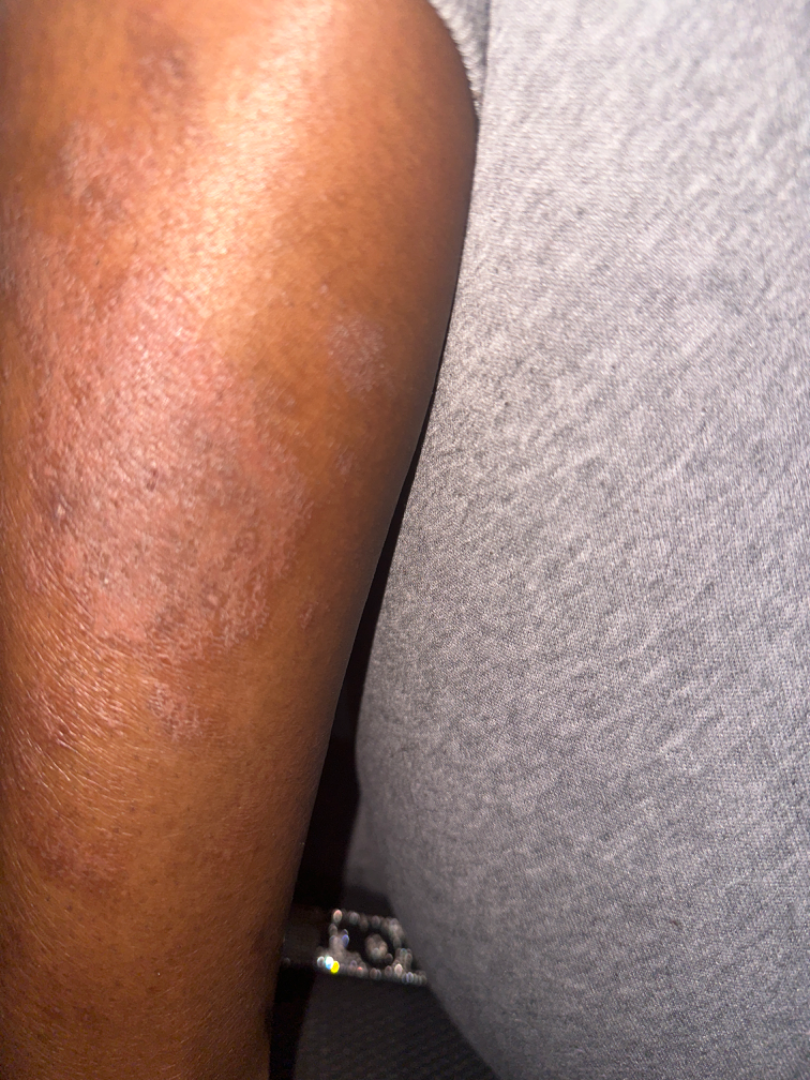The photograph is a close-up of the affected area. The patient reports itching, bothersome appearance, enlargement, darkening and burning. Fitzpatrick V; non-clinician graders estimated Monk Skin Tone 6 or 7 (two reviewer pools). The contributor is a female aged 18–29. The leg and arm are involved. Self-categorized by the patient as a rash. One reviewing dermatologist: Psoriasis and Eczema were considered with similar weight; less probable is Cutaneous T Cell Lymphoma.